Reported lesion symptoms include bothersome appearance, enlargement and itching · the patient considered this a rash · present for one to four weeks · the lesion involves the leg, top or side of the foot, arm, back of the torso and front of the torso · no constitutional symptoms were reported · this is a close-up image: 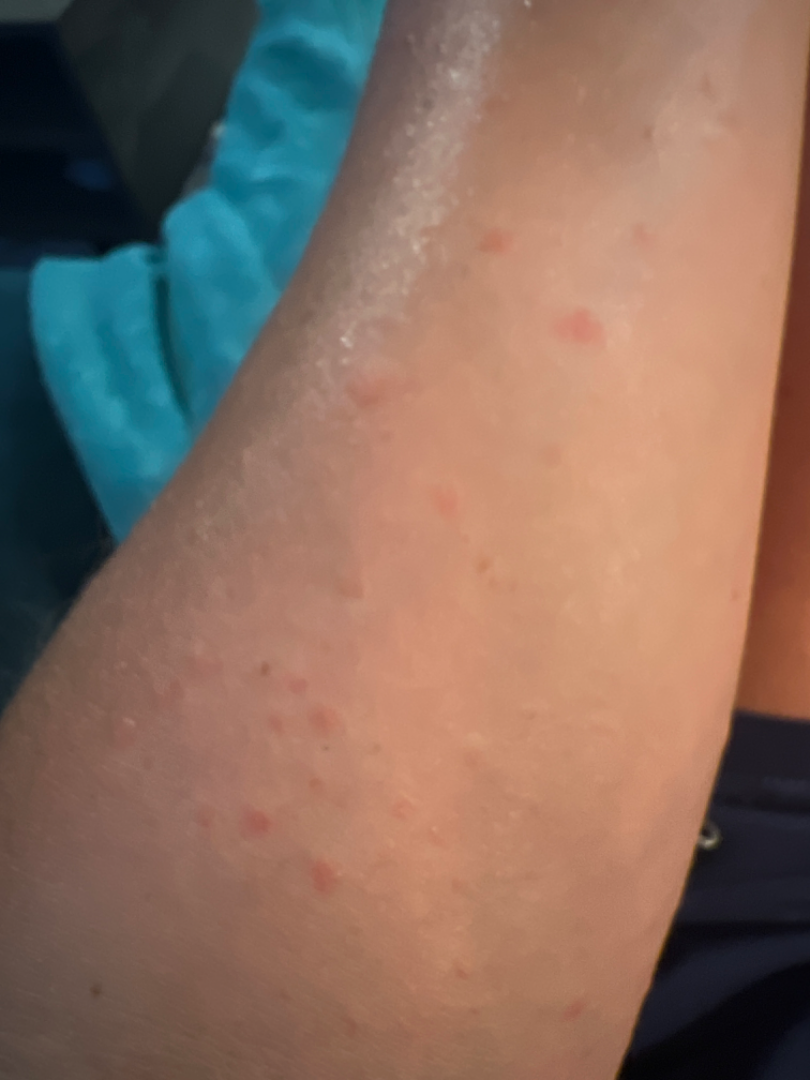No differential diagnosis could be assigned on photographic review.